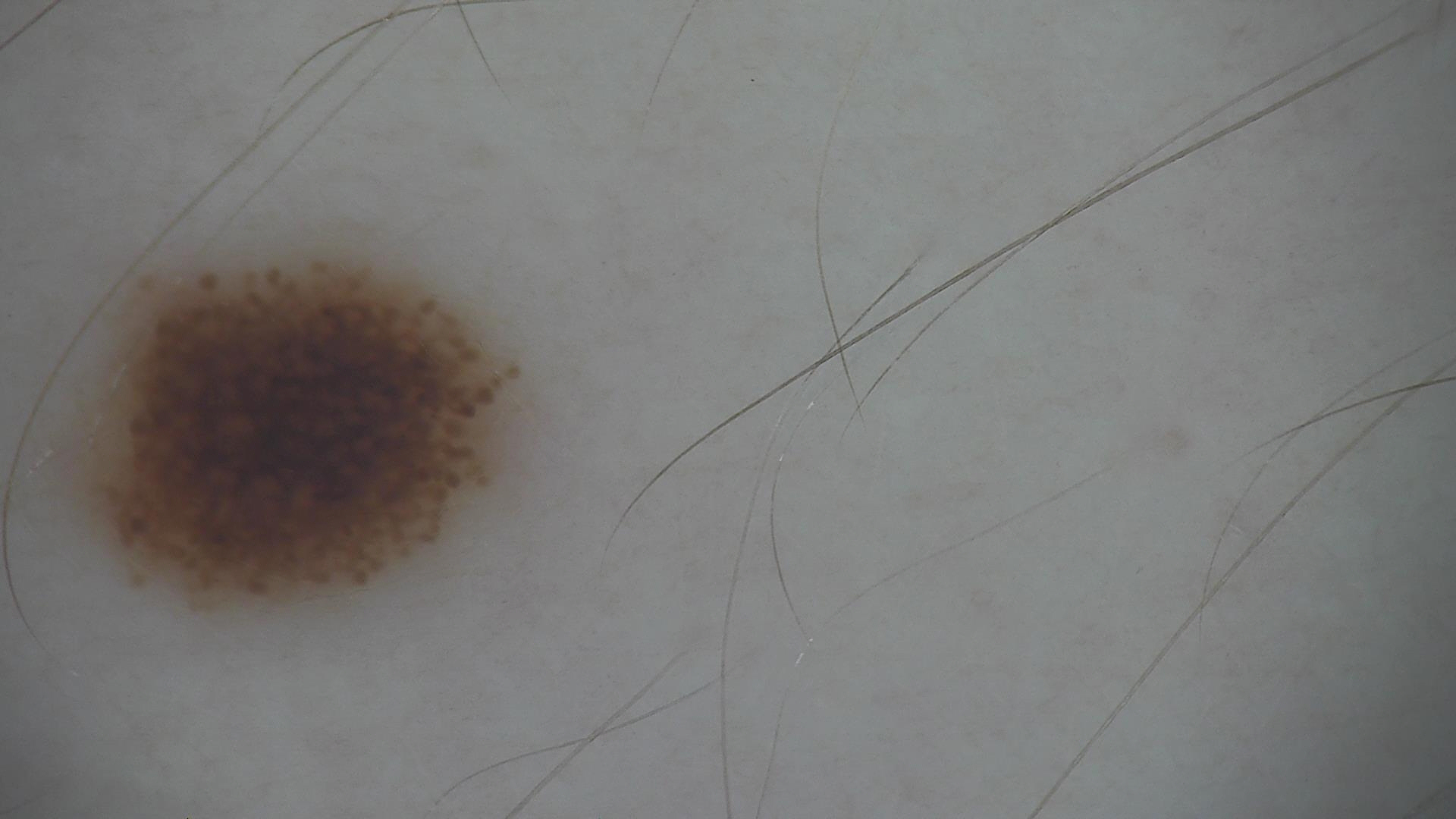image: dermatoscopy
diagnosis:
  name: dysplastic junctional nevus
  code: jd
  malignancy: benign
  super_class: melanocytic
  confirmation: expert consensus